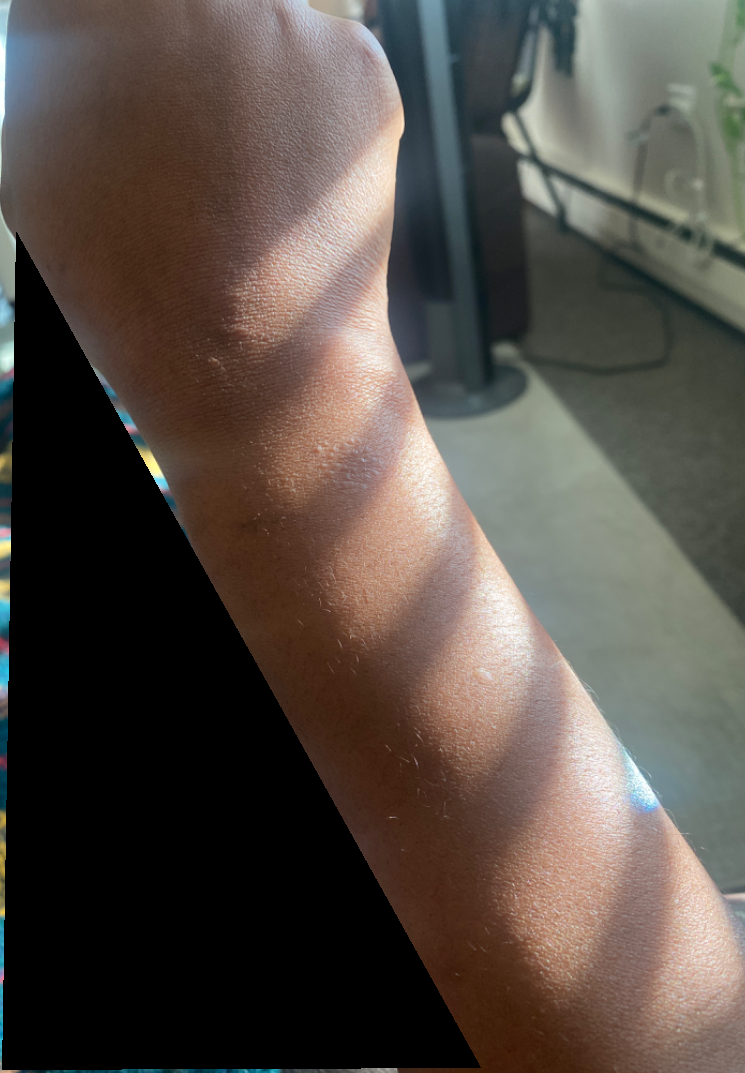Q: What was the assessment?
A: unable to determine